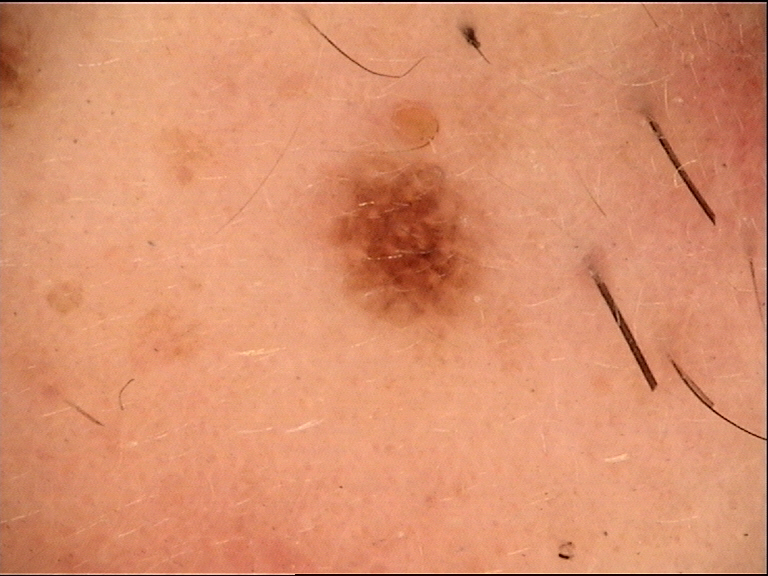A dermoscopic image of a skin lesion.
The diagnostic label was a compound lesion — a Miescher nevus.